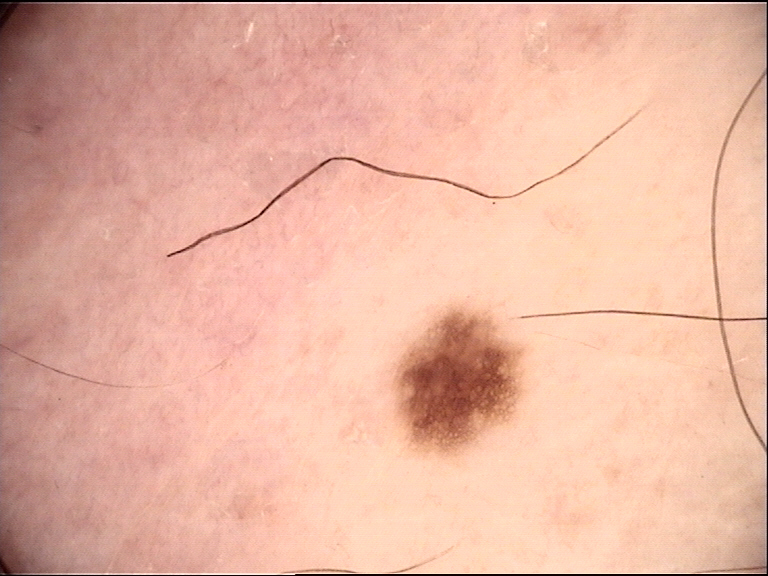Dermoscopy of a skin lesion.
Labeled as a dysplastic junctional nevus.